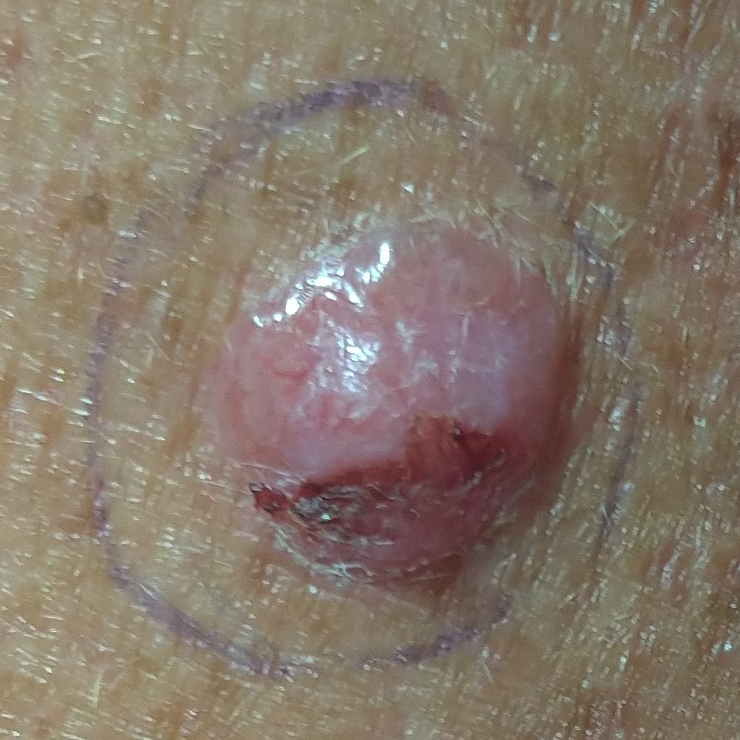The chart notes prior malignancy (patient or family) and alcohol use.
A female subject age 54.
Recorded as Fitzpatrick phototype III.
A clinical photograph of a skin lesion.
The lesion is located on a forearm.
The lesion measures 15 × 13 mm.
By the patient's account, the lesion itches, has bled, is elevated, and has grown.
Histopathological examination showed a malignant skin lesion — a basal cell carcinoma.